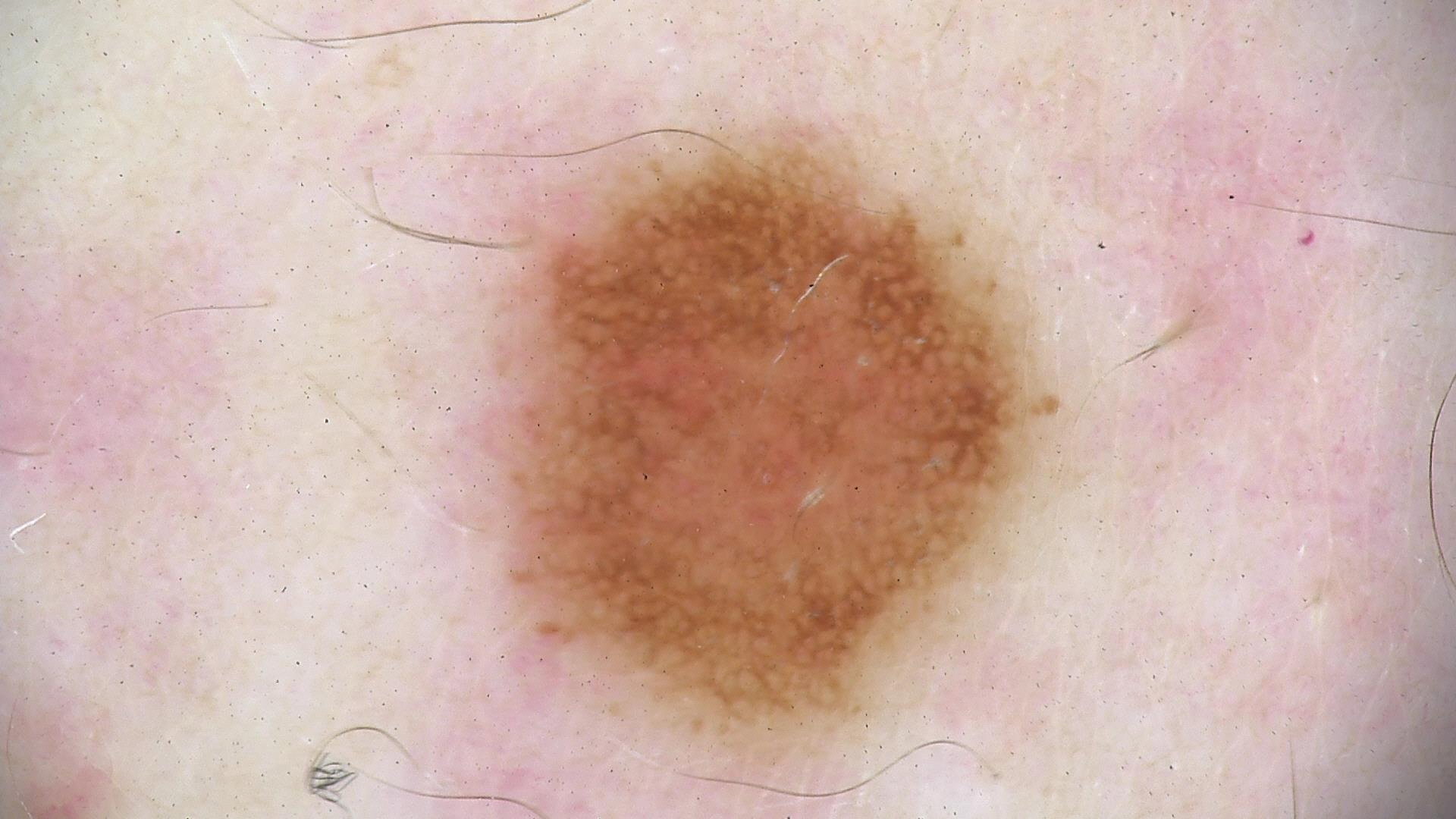A dermatoscopic image of a skin lesion.
The architecture is that of a banal lesion.
The diagnostic label was a compound nevus.